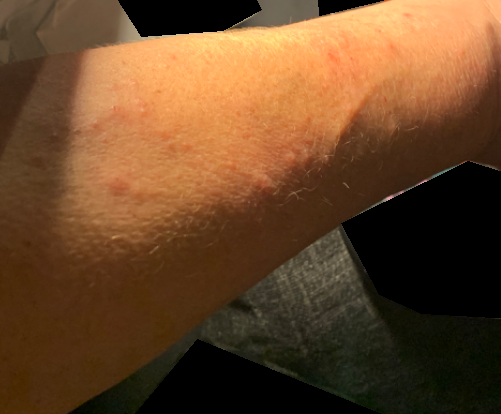Patient information:
The photo was captured at a distance. The arm is involved. The subject is female.
Review:
On independent review by the dermatologists, Contact dermatitis (considered); Allergic Contact Dermatitis (considered); Folliculitis (considered).